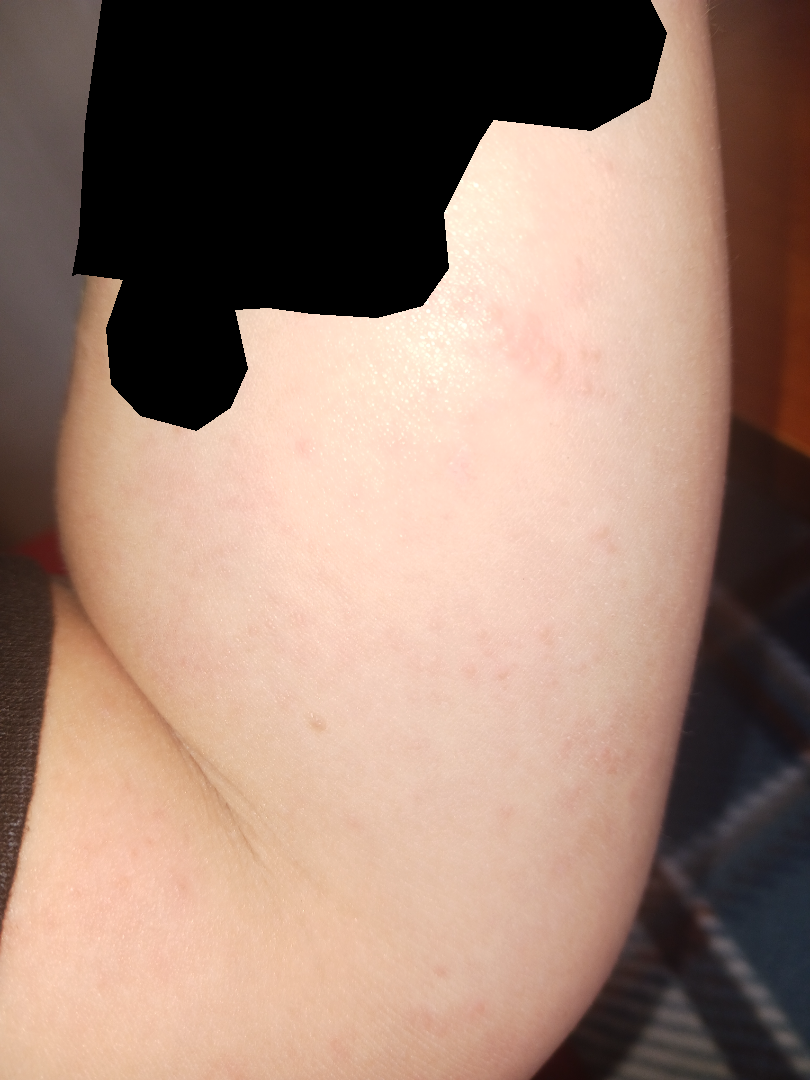Notes:
* differential diagnosis: Eczema and Allergic Contact Dermatitis were considered with similar weight